A clinical photo of a skin lesion taken with a smartphone: 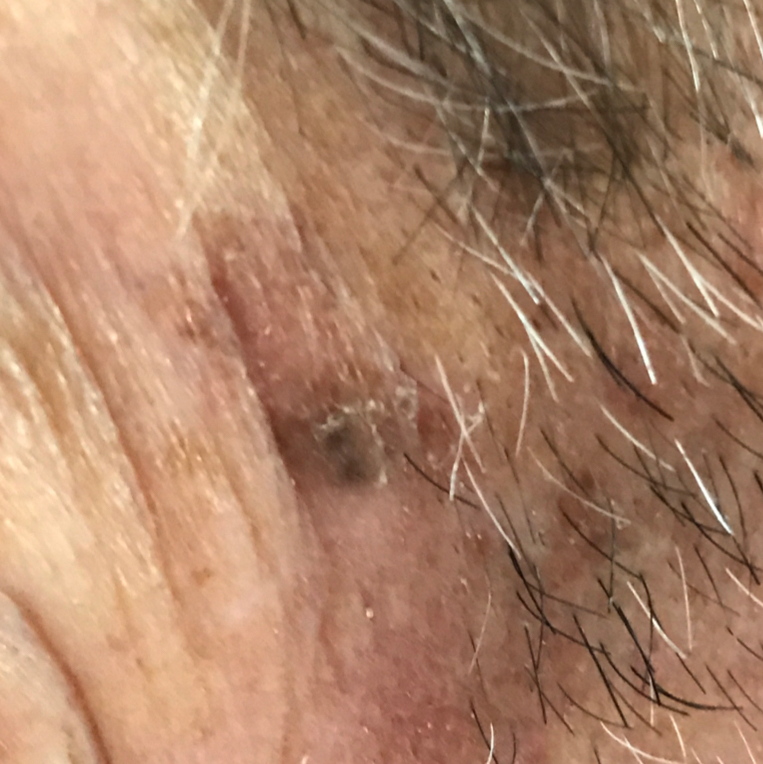The patient reports that the lesion itches and is elevated. Consistent with a benign skin lesion — a seborrheic keratosis.